The subject is male. The photograph is a close-up of the affected area. The lesion involves the back of the hand.
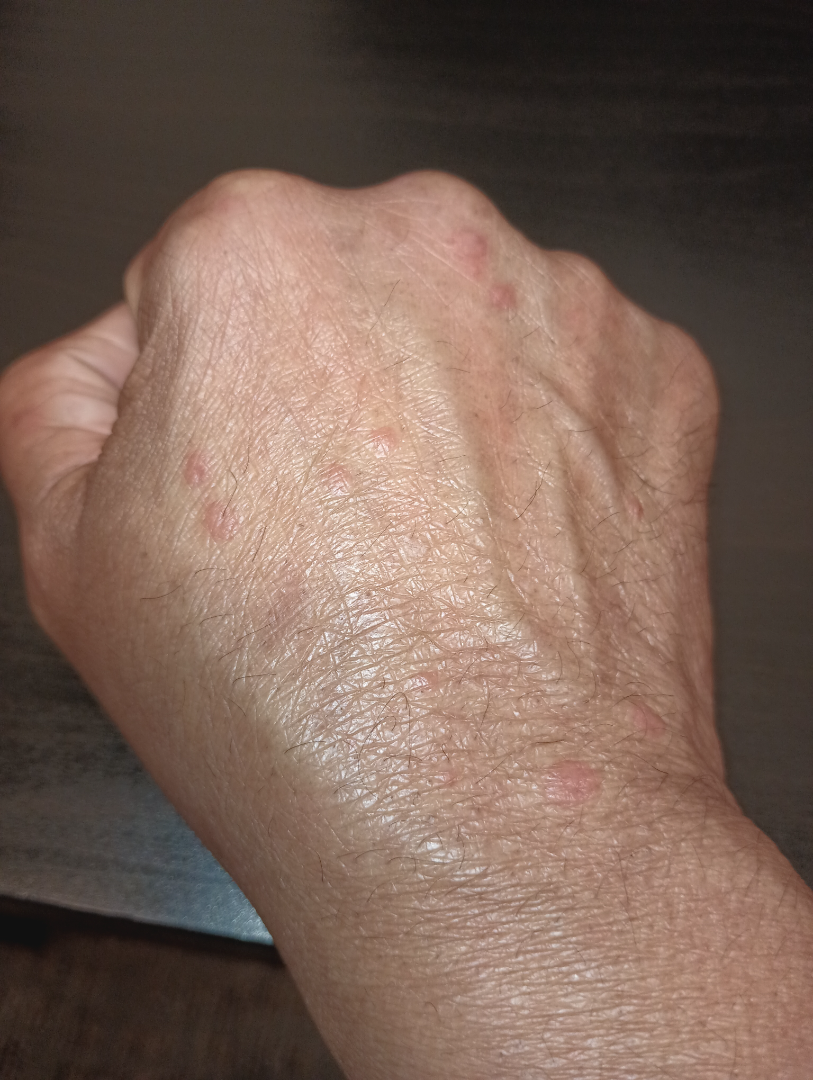| field | value |
|---|---|
| patient-reported symptoms | itching and bothersome appearance |
| self-categorized as | a rash |
| associated systemic symptoms | none reported |
| duration | less than one week |
| dermatologist impression | reviewed remotely by three dermatologists: the differential includes Granuloma annulare and Insect Bite, with no clear leading consideration; less likely is Verruca vulgaris; less probable is Cutaneous sarcoidosis |